Located on the leg · the patient indicates the lesion is raised or bumpy · the patient is 70–79, female · symptoms reported: bothersome appearance, itching, pain and enlargement · a close-up photograph · self-categorized by the patient as a rash · reported duration is one to four weeks: 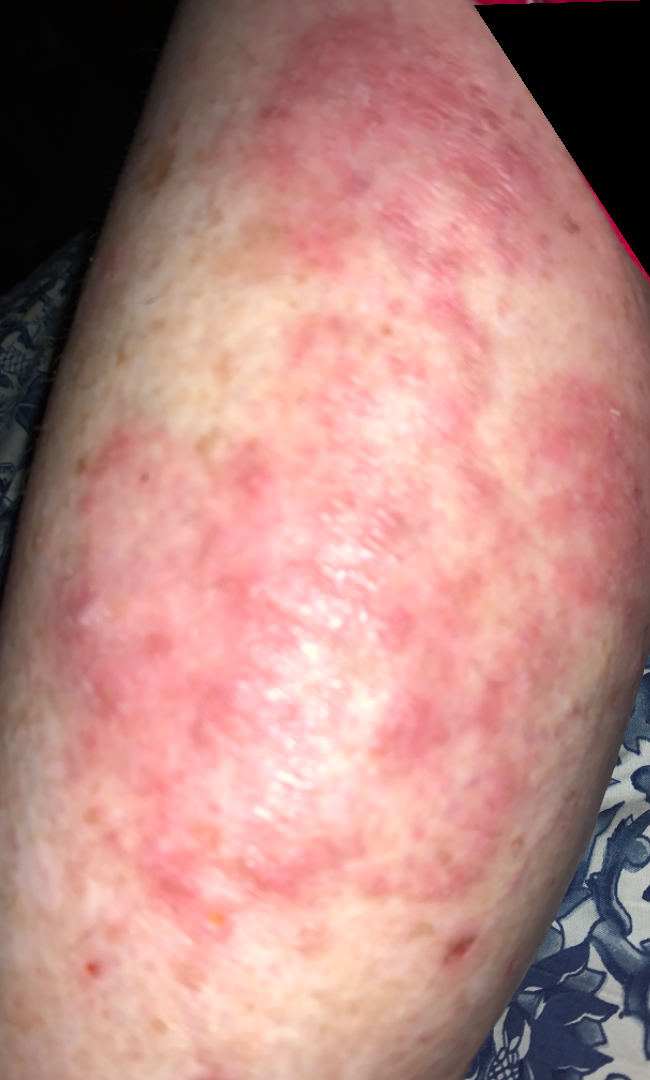Tinea (most likely); Psoriasis (possible); Eczema (possible).